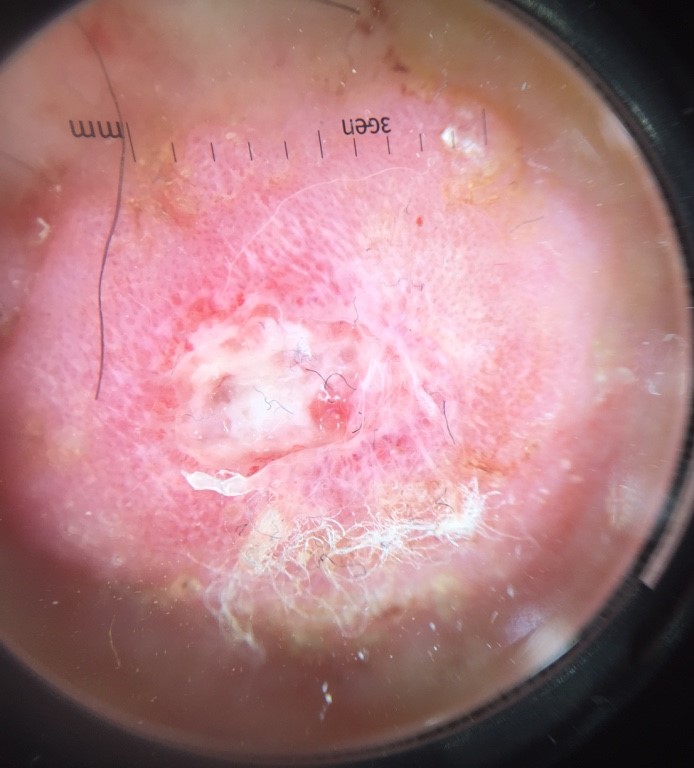Summary: A dermoscopic image of a skin lesion. This is a keratinocytic lesion. Conclusion: Histopathologically confirmed as a squamous cell carcinoma.